The photograph was taken at an angle:
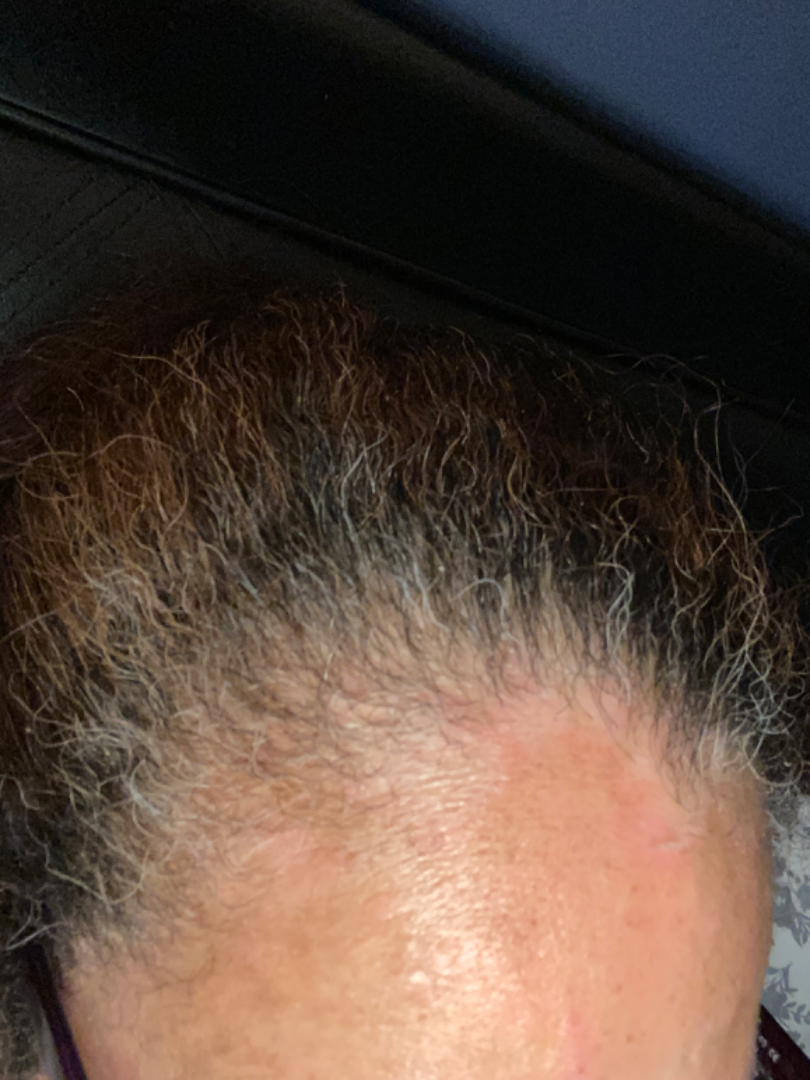| feature | finding |
|---|---|
| assessment | indeterminate |